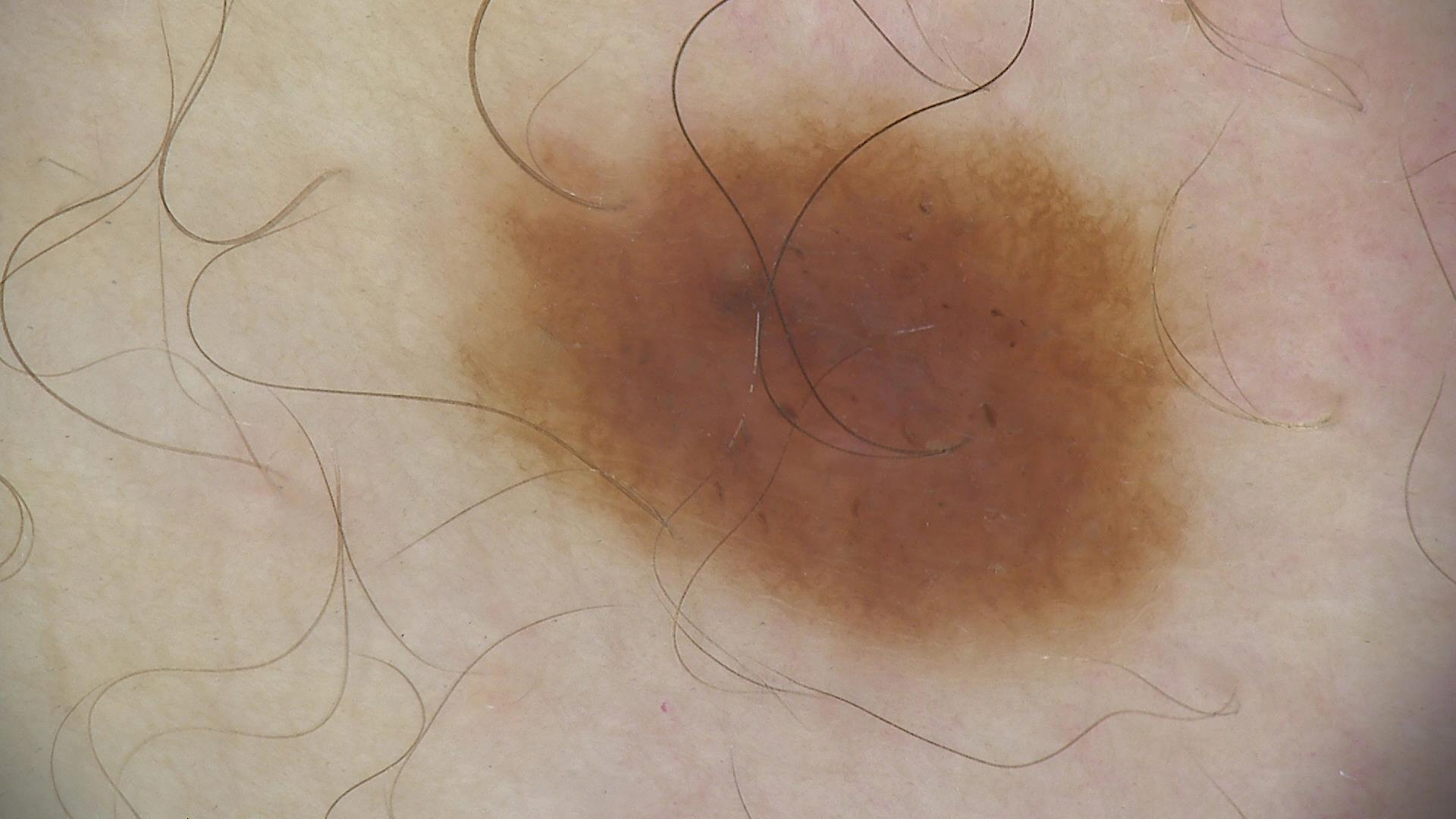This is a banal lesion. Diagnosed as a compound nevus.